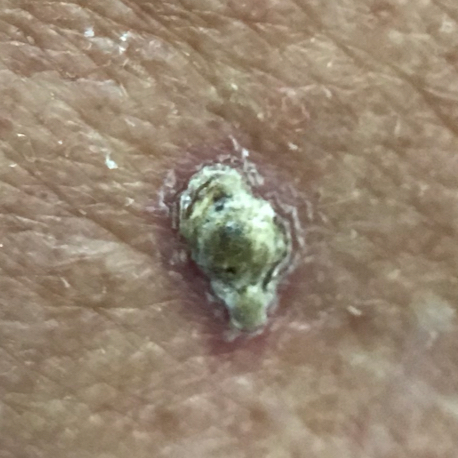Located on the back. The biopsy diagnosis was a basal cell carcinoma.